A dermoscopic close-up of a skin lesion.
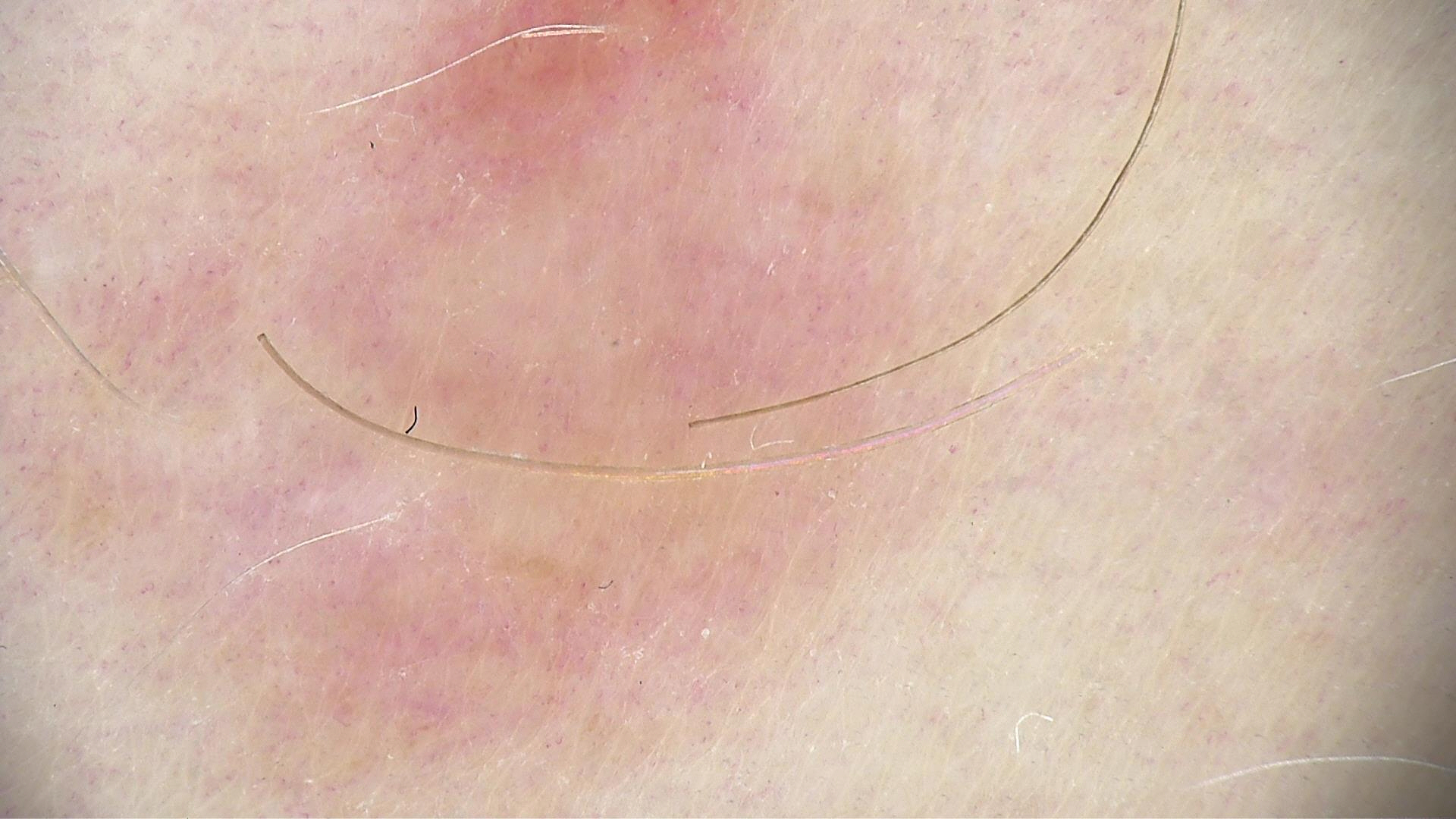The architecture is that of a banal lesion. Consistent with a junctional nevus.